The affected area is the leg; an image taken at an angle; female patient, age 40–49.
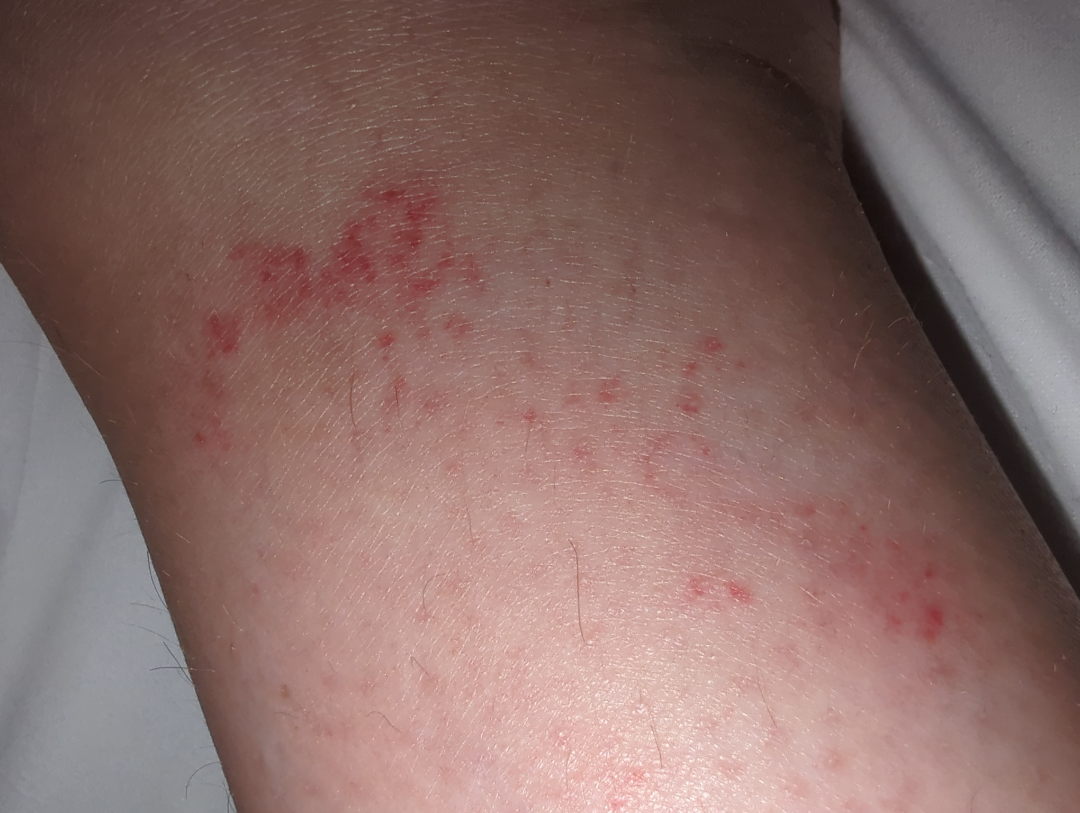On dermatologist assessment of the image: the impression was split between Eczema and Irritant Contact Dermatitis.